The photo was captured at an angle, the front of the torso is involved — 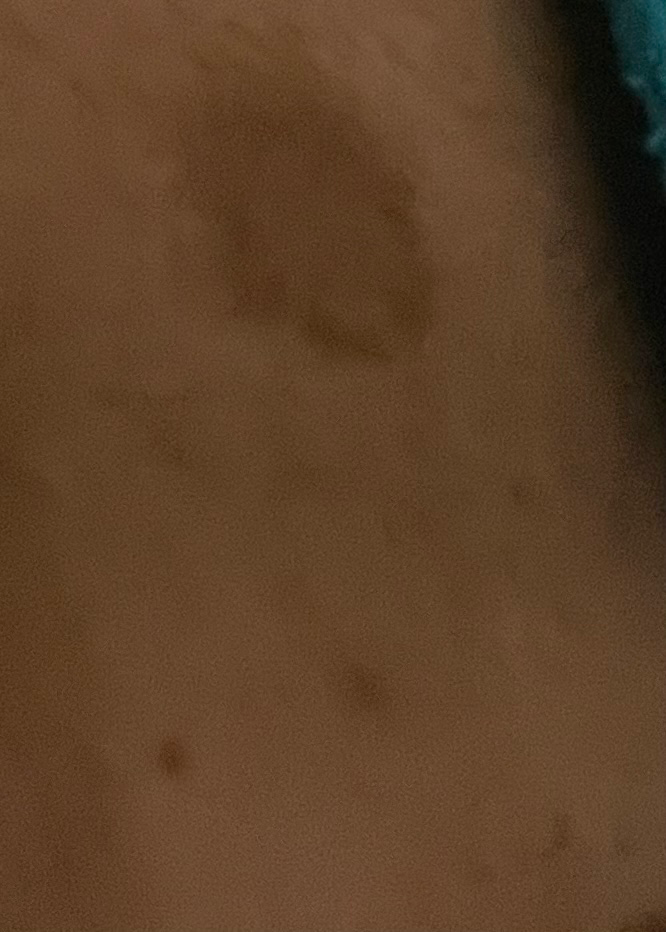The reviewing dermatologist was unable to assign a differential diagnosis from the image.
Present for more than one year.
Texture is reported as flat.
Lay reviewers estimated MST 3 or 4.
The lesion is associated with itching, pain, bothersome appearance and enlargement.